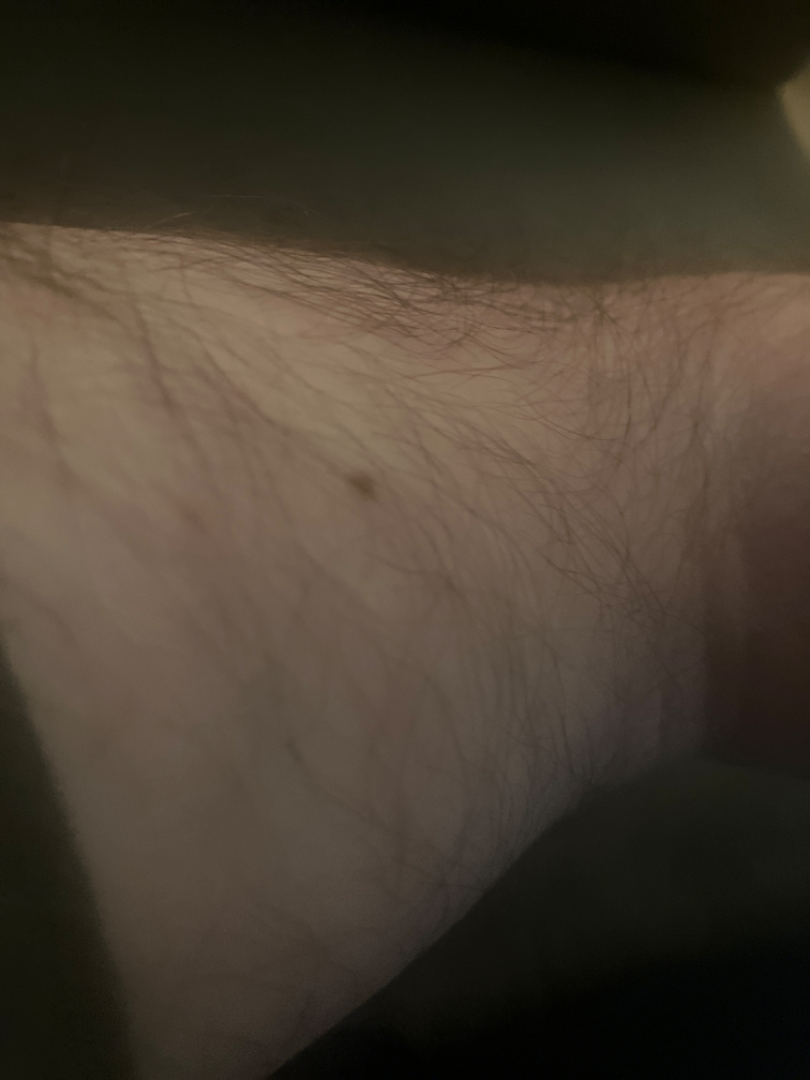Case summary:
• assessment: could not be assessed
• view: close-up